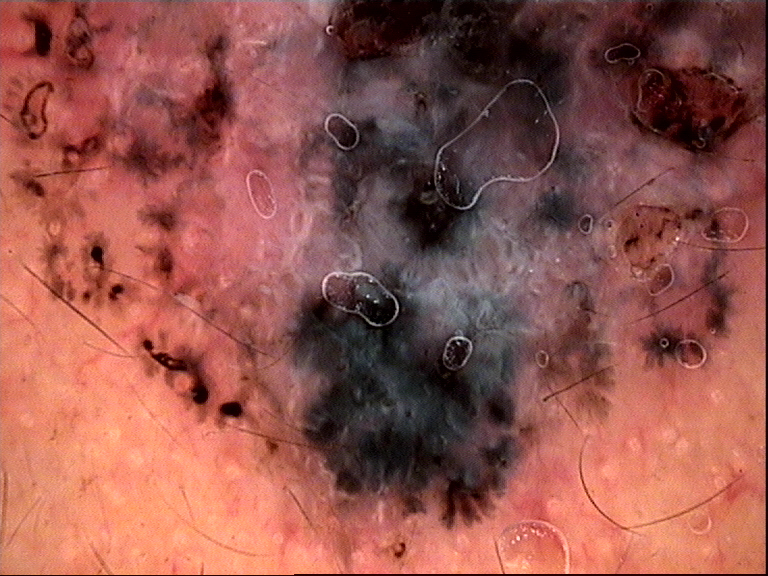Q: What did the workup show?
A: basal cell carcinoma (biopsy-proven)